The arm is involved; close-up view — 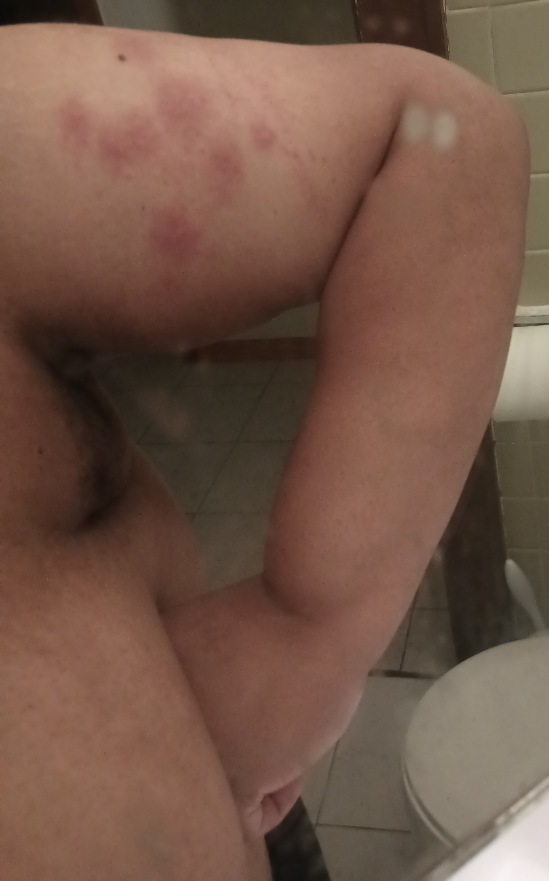{
  "symptoms": "itching",
  "patient_category": "a rash",
  "systemic_symptoms": "none reported",
  "texture": "raised or bumpy",
  "duration": "less than one week",
  "differential": {
    "leading": [
      "Urticaria"
    ],
    "considered": [
      "Insect Bite",
      "Hypersensitivity"
    ]
  }
}